The chart notes prior skin cancer (patient or family) · the patient was assessed as FST III · a clinical photograph of a skin lesion — 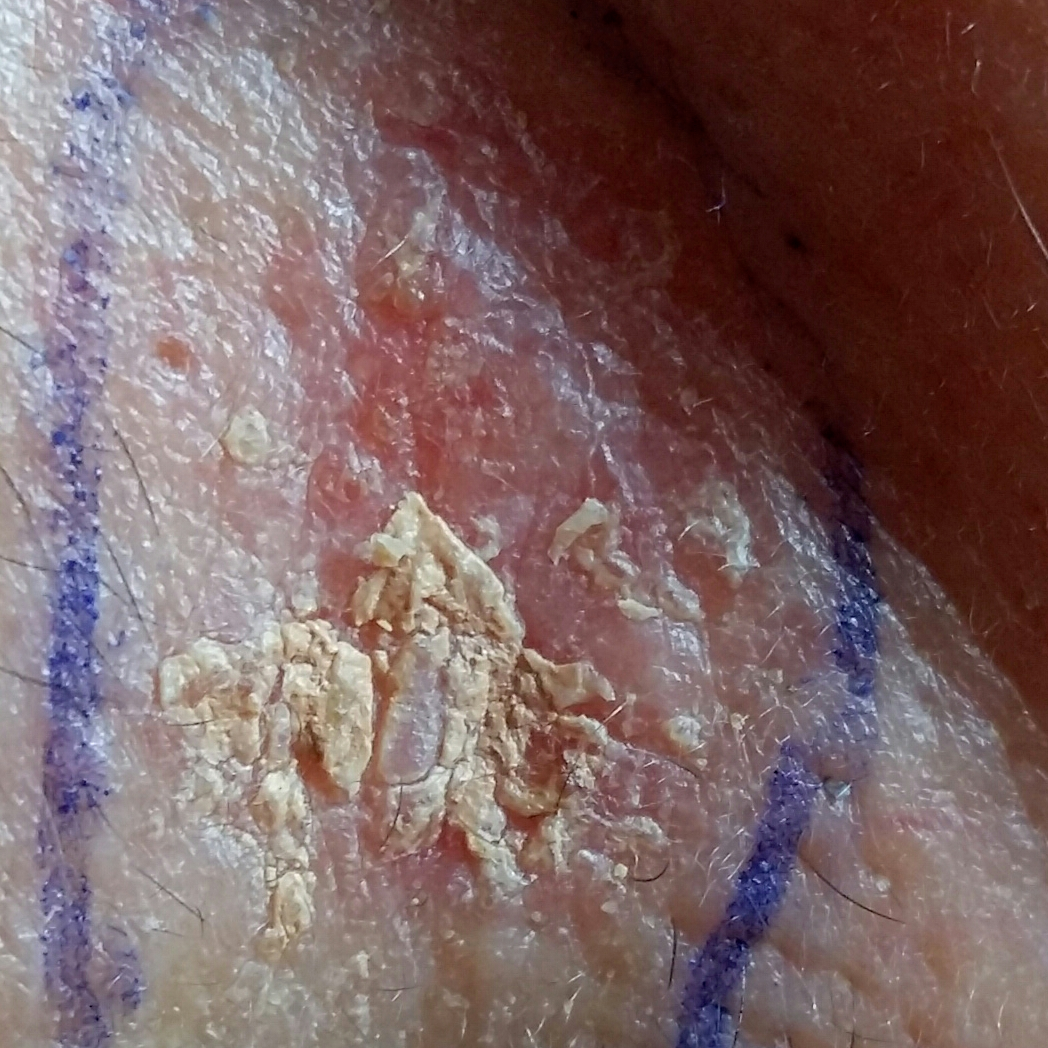The lesion is on the face. The lesion measures 15 × 9 mm. Per patient report, the lesion itches, but does not hurt. On biopsy, the diagnosis was a basal cell carcinoma.